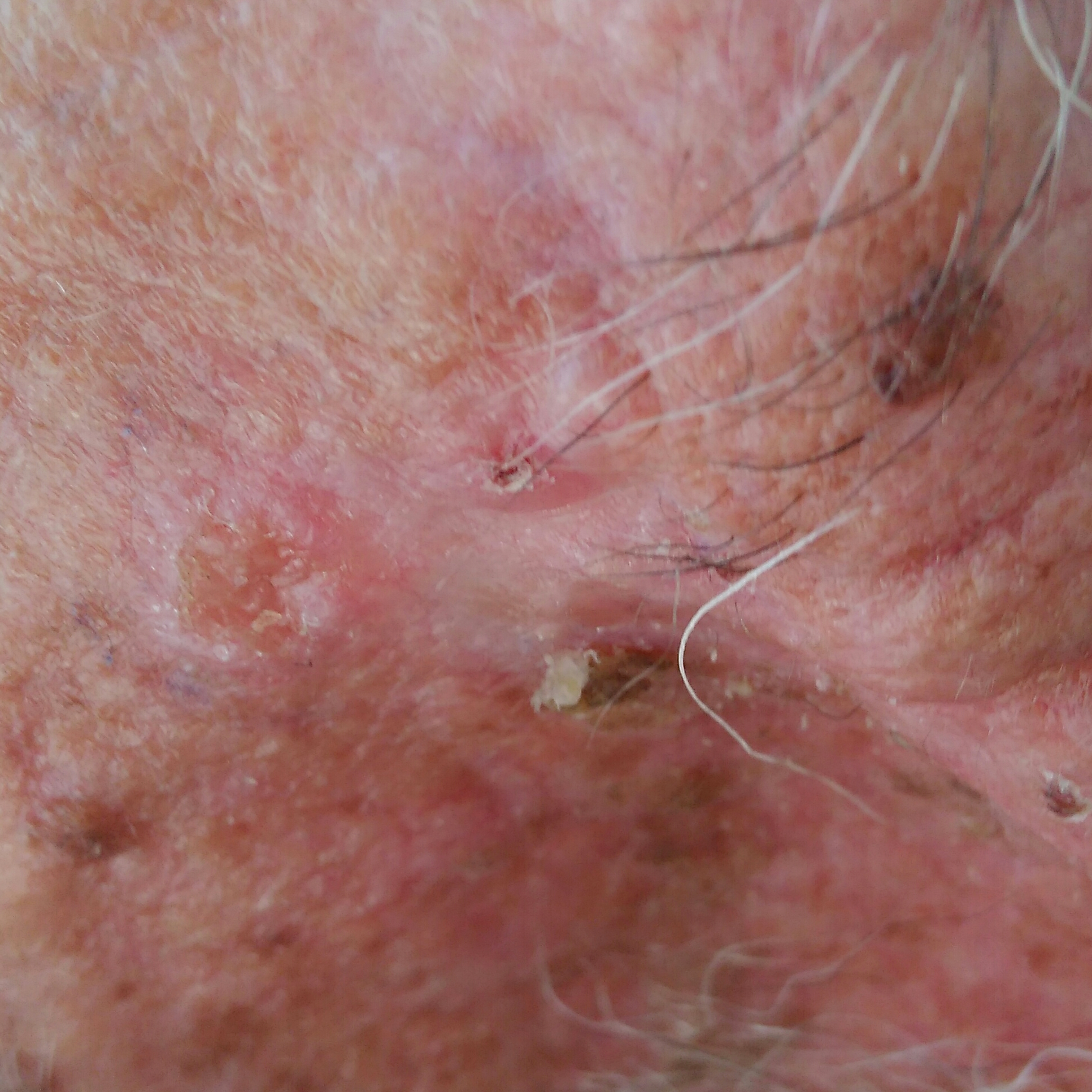A male subject 61 years of age. Skin type II. History notes tobacco use and alcohol use. A clinical close-up photograph of a skin lesion. The lesion involves the face. The lesion measures approximately 19 × 8 mm. By the patient's account, the lesion hurts, is elevated, itches, and has bled. Histopathologically confirmed as a basal cell carcinoma.